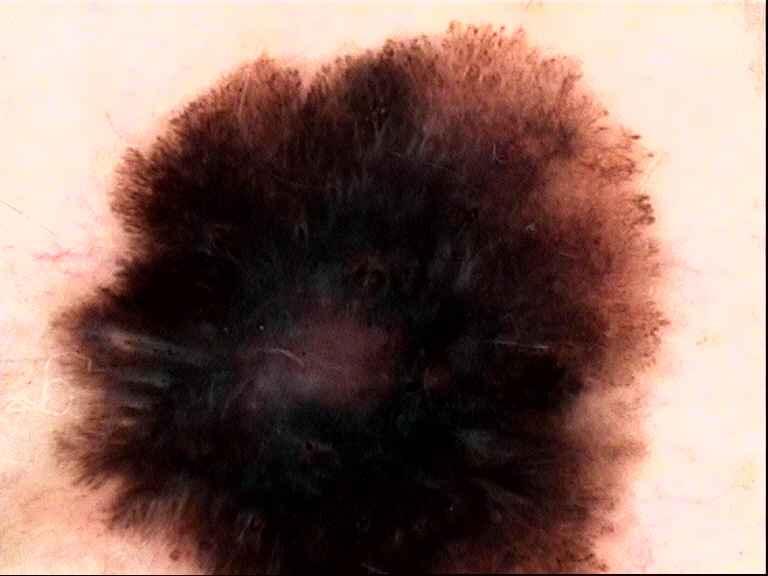image = dermoscopy; diagnostic label = melanoma (biopsy-proven).